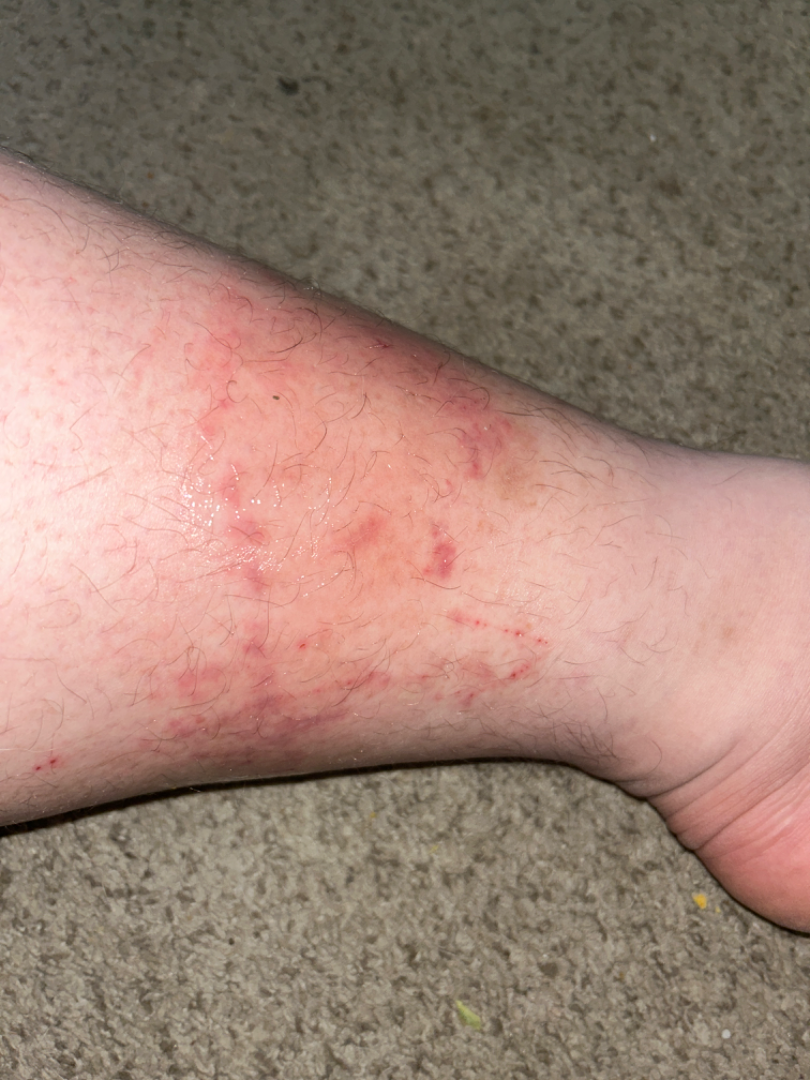Symptoms reported: itching and enlargement. The patient considered this a rash. No relevant systemic symptoms. The patient notes the lesion is raised or bumpy. An image taken at a distance. Present for one to four weeks. Located on the leg. Male patient, age 18–29. The reviewing clinician's impression was: most consistent with Allergic Contact Dermatitis.